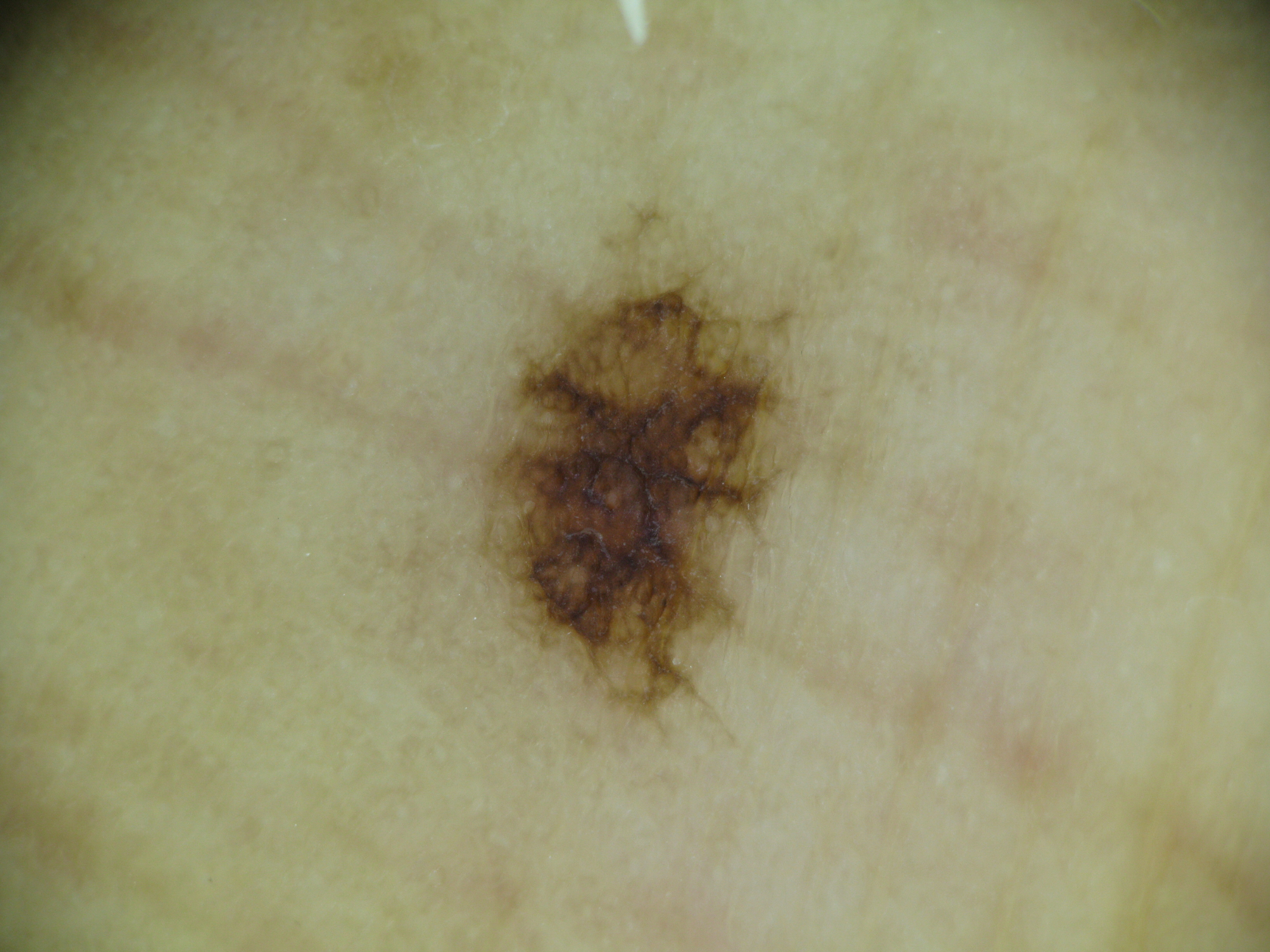Q: What kind of image is this?
A: dermatoscopy
Q: What was the diagnostic impression?
A: acral dysplastic junctional nevus (expert consensus)